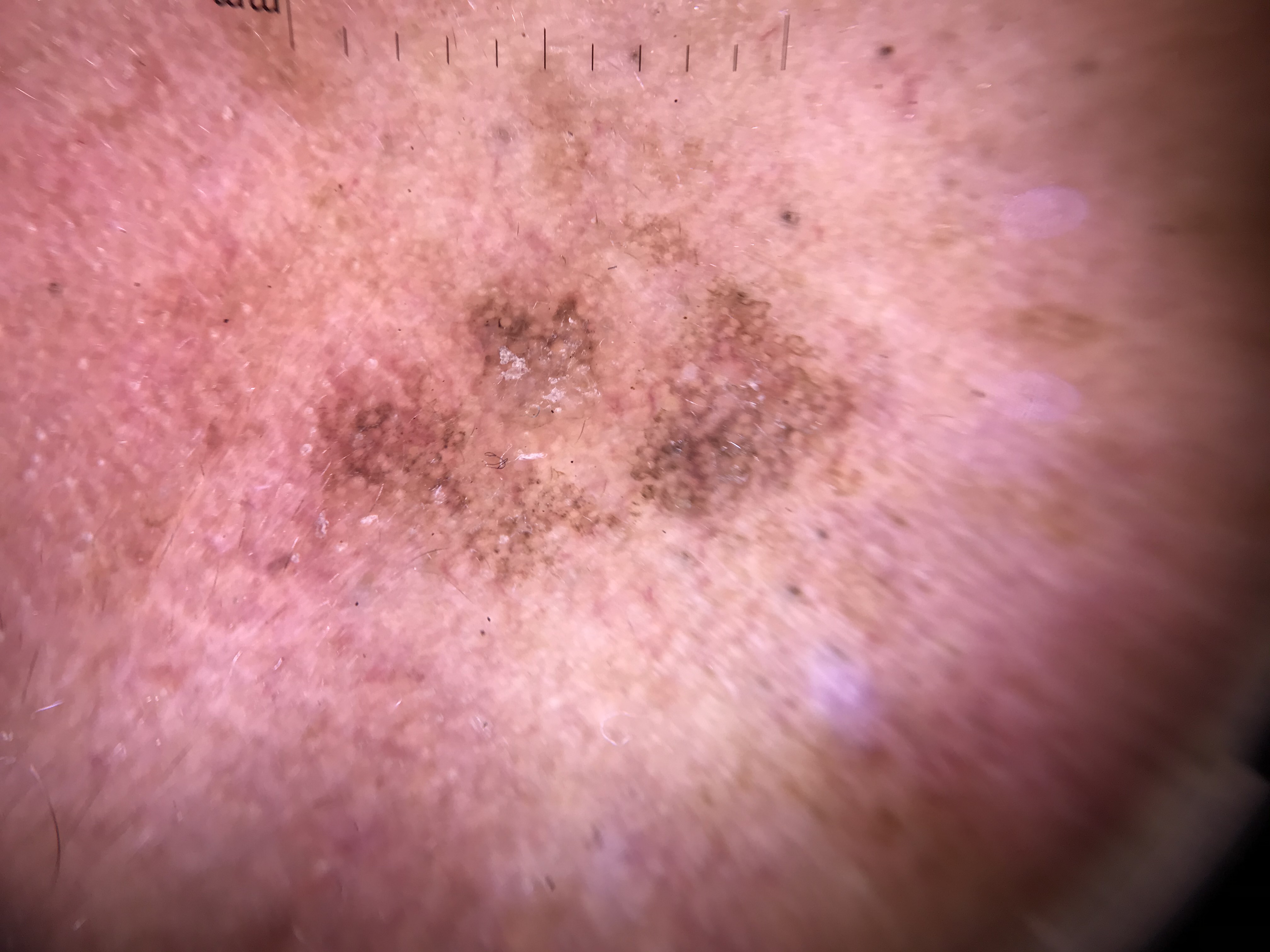Diagnosed as a seborrheic keratosis.